This is a dermoscopic photograph of a skin lesion. A female subject aged around 30.
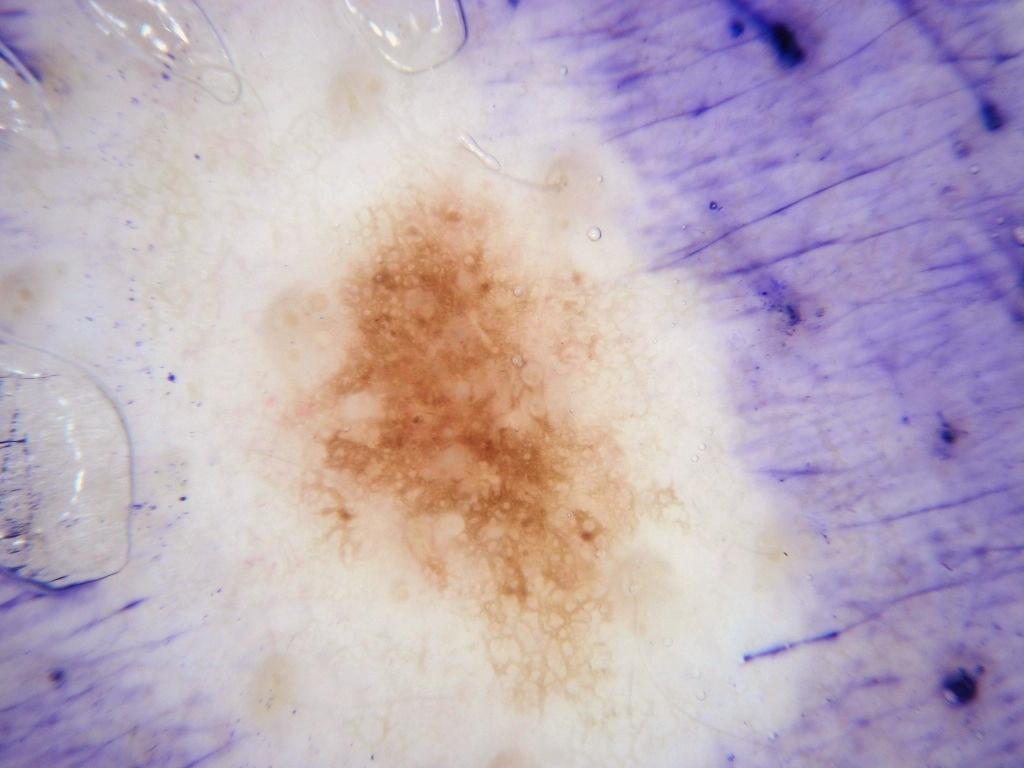  dermoscopic_features:
    present:
      - pigment network
    absent:
      - globules
      - streaks
      - milia-like cysts
      - negative network
  lesion_location:
    bbox_xyxy:
      - 257
      - 173
      - 674
      - 733
  diagnosis:
    name: melanocytic nevus
    malignancy: benign
    lineage: melanocytic
    provenance: clinical